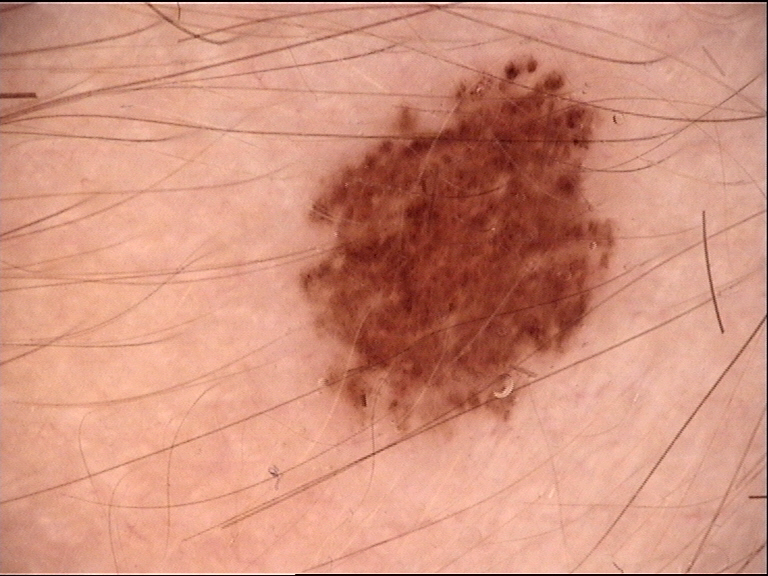Consistent with a benign lesion — a dysplastic junctional nevus.